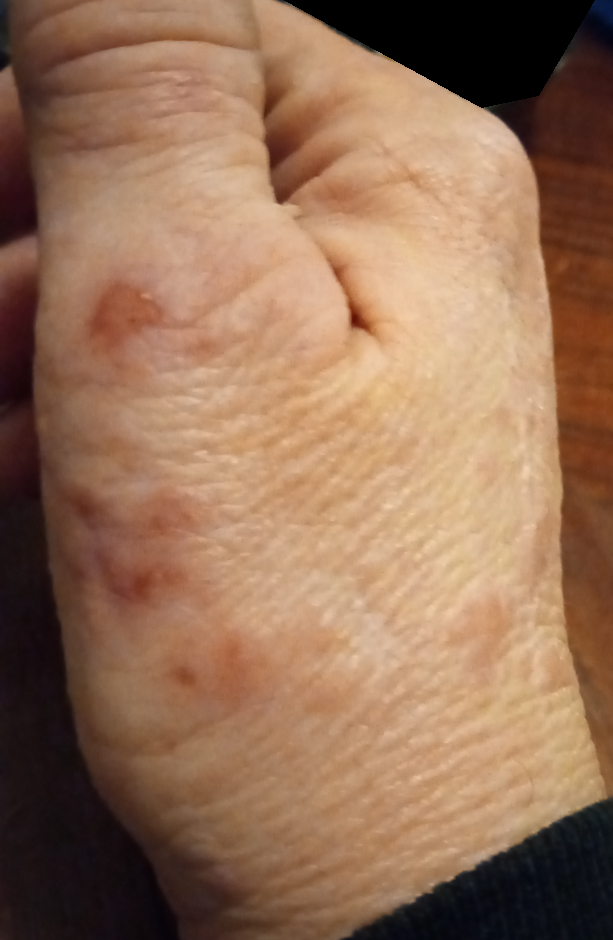view — close-up
differential diagnosis — the leading consideration is Eczema; an alternative is Infected eczema; less probable is Herpes Simplex